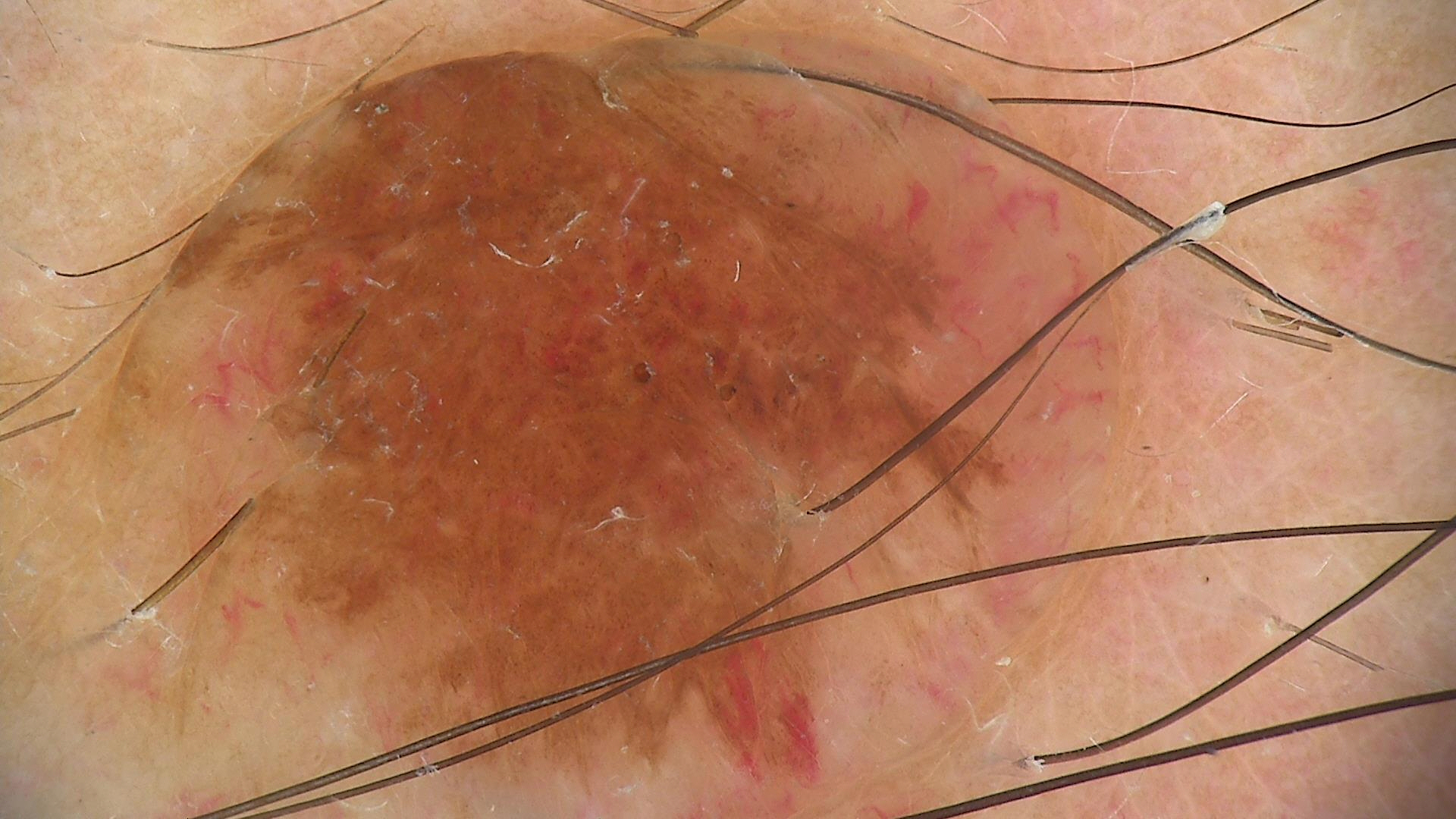Findings:
A dermoscopic photograph of a skin lesion. The architecture is that of a banal lesion.
Conclusion:
Diagnosed as a dermal nevus.